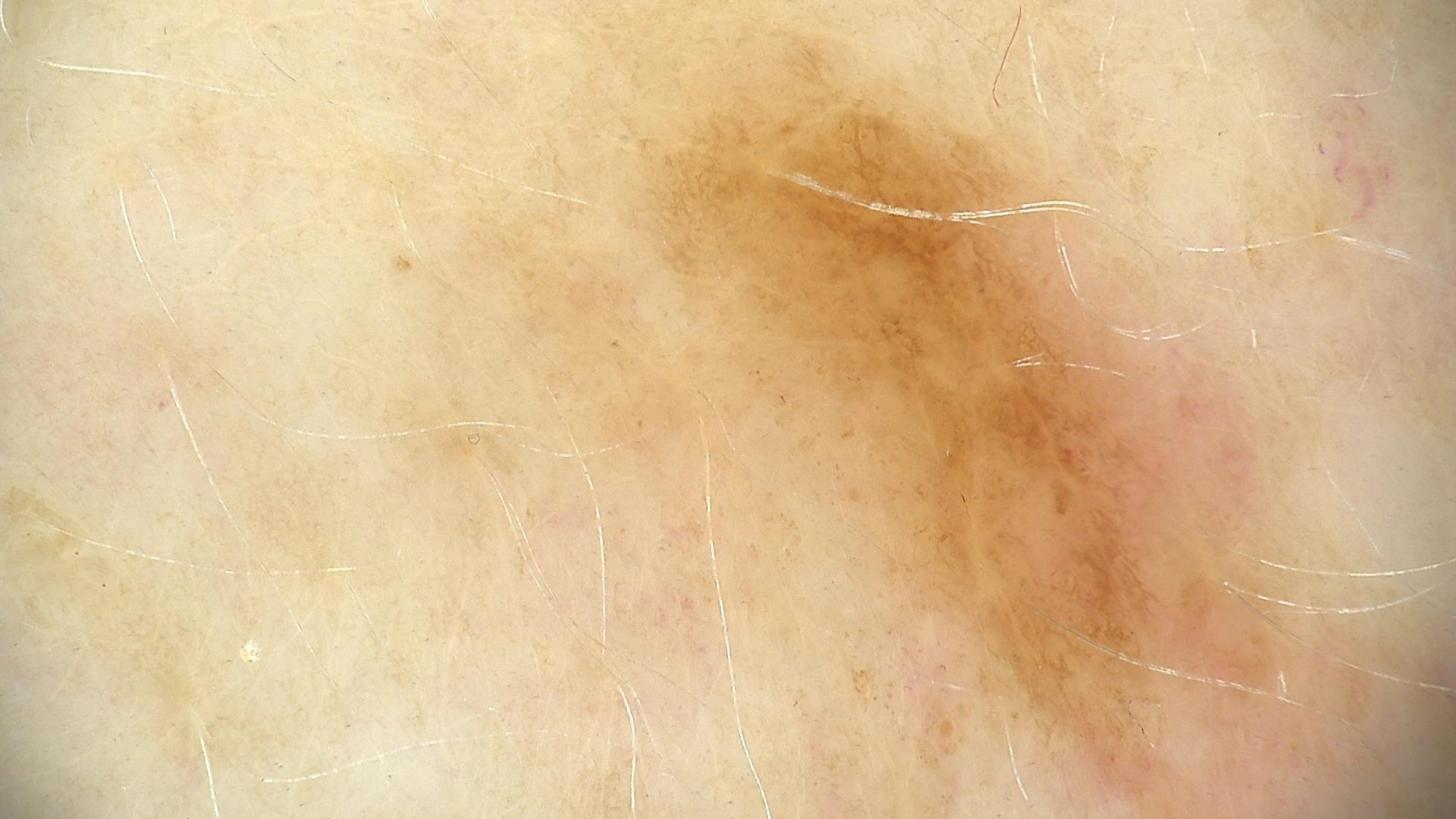A dermoscopic image of a skin lesion.
The diagnostic label was a dysplastic junctional nevus.